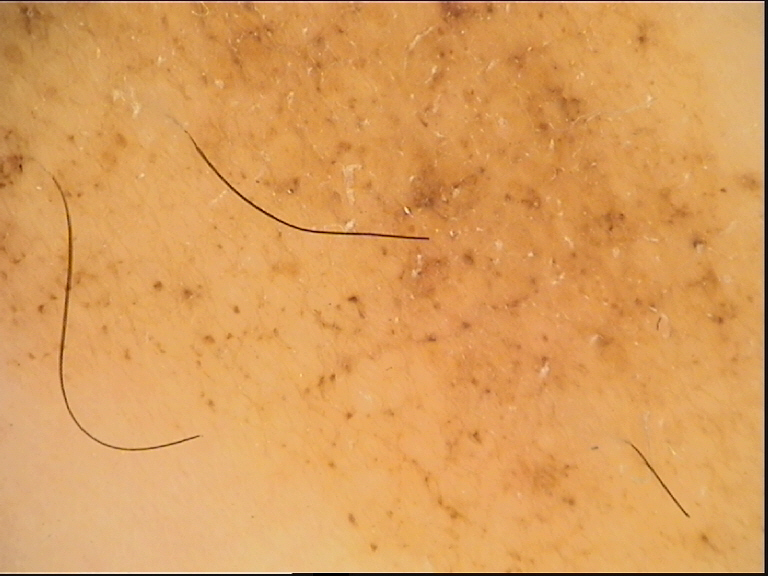{"diagnosis": {"name": "congenital junctional nevus", "code": "cjb", "malignancy": "benign", "super_class": "melanocytic", "confirmation": "expert consensus"}}